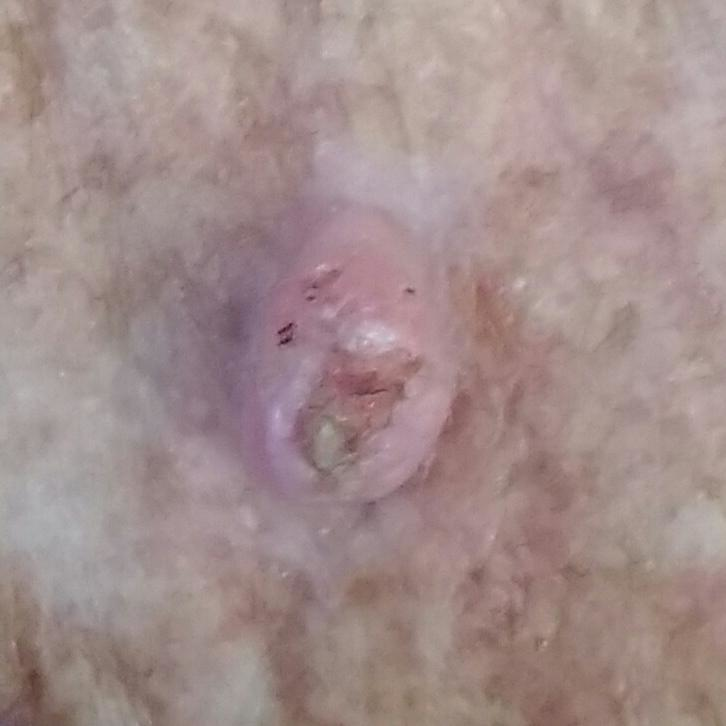image — smartphone clinical photo
skin type — III
risk factors — prior malignancy (patient or family)
body site — the nose
pathology — basal cell carcinoma (biopsy-proven)